Texture is reported as rough or flaky and raised or bumpy. Located on the back of the hand. This image was taken at an angle. Self-categorized by the patient as a growth or mole:
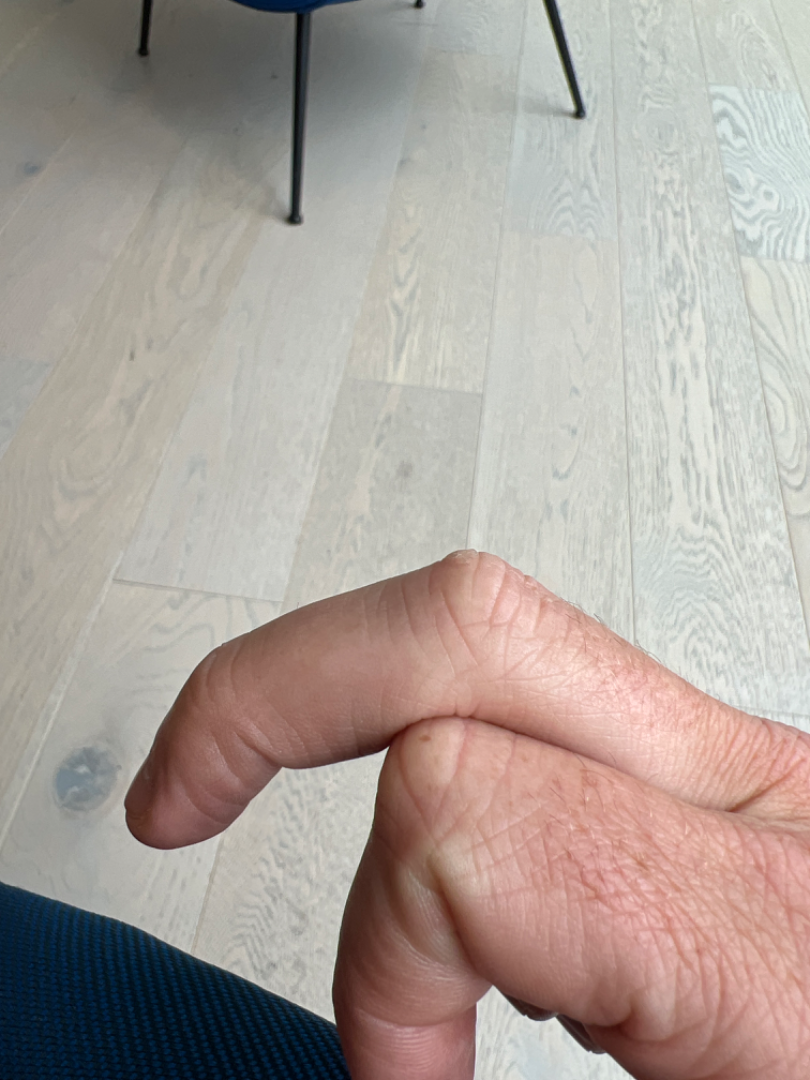On remote review of the image: in keeping with Verruca vulgaris.